Dermoscopy of a skin lesion.
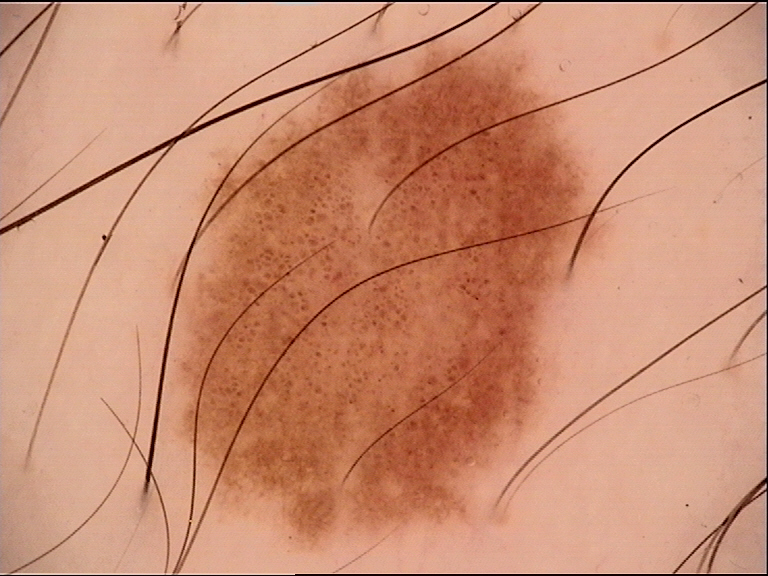The diagnostic label was a benign lesion — a dysplastic junctional nevus.